A dermoscopic close-up of a skin lesion: 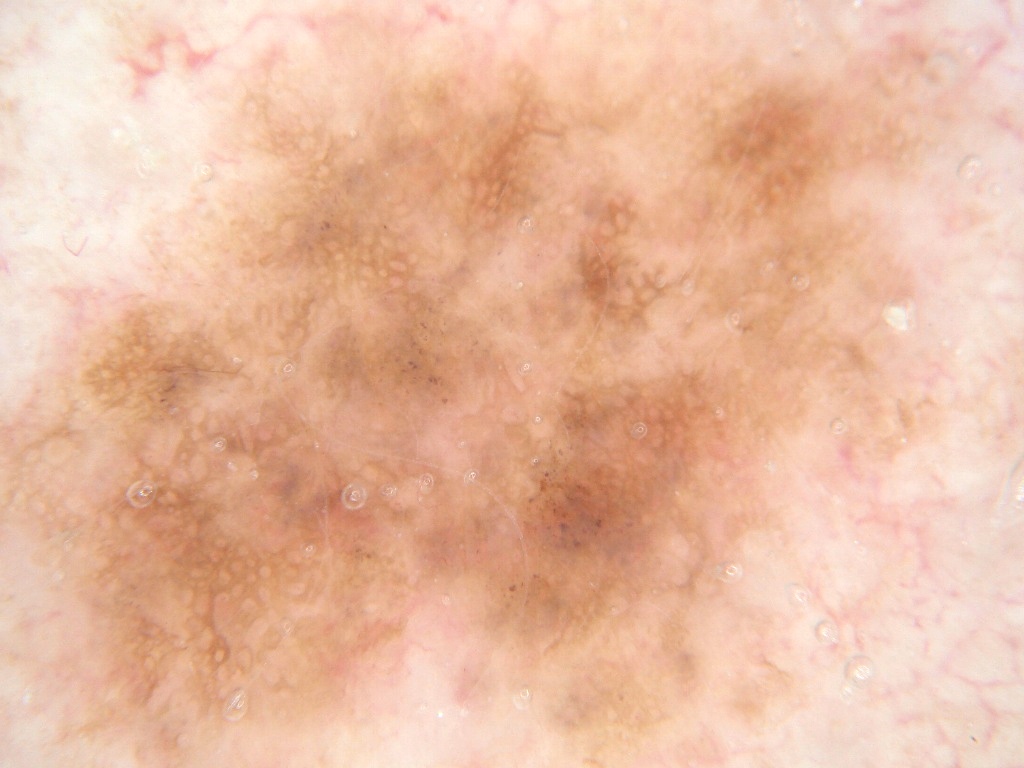location: spans the dermoscopic field, impression: a benign skin lesion.